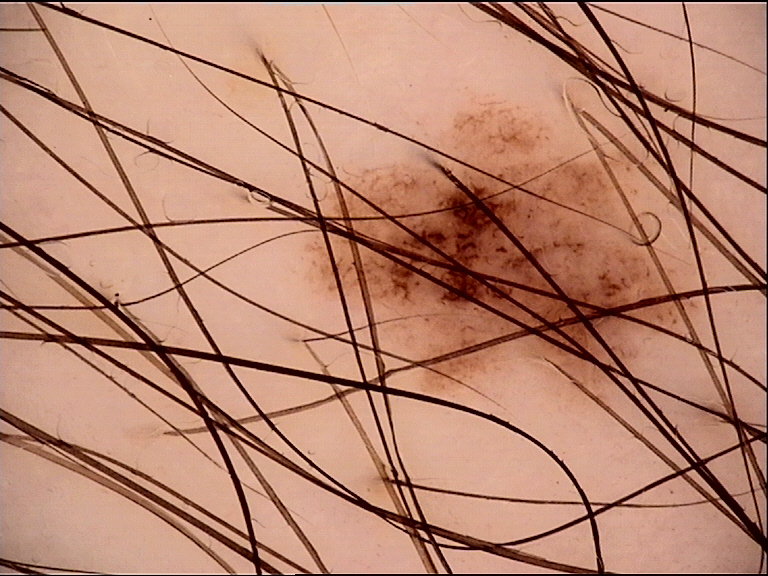Impression:
Consistent with a dysplastic junctional nevus.